The head or neck is involved. This image was taken at an angle. Male patient, age 50–59:
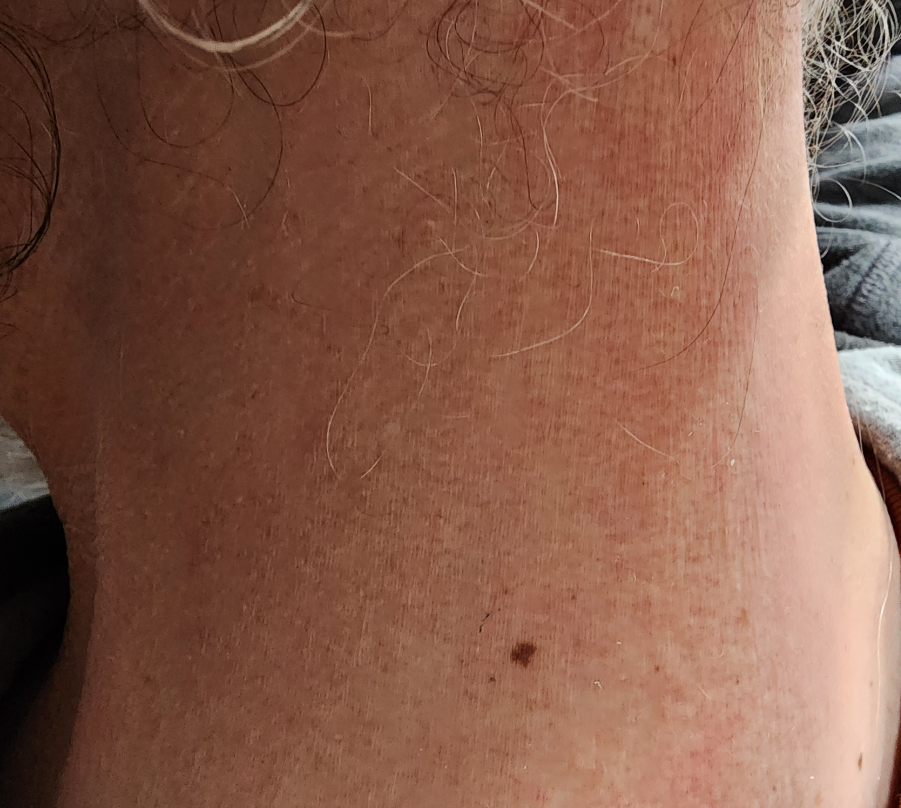Case summary:
• differential · the leading consideration is Seborrheic Dermatitis; possibly Psoriasis